A dermoscopic photograph of a skin lesion.
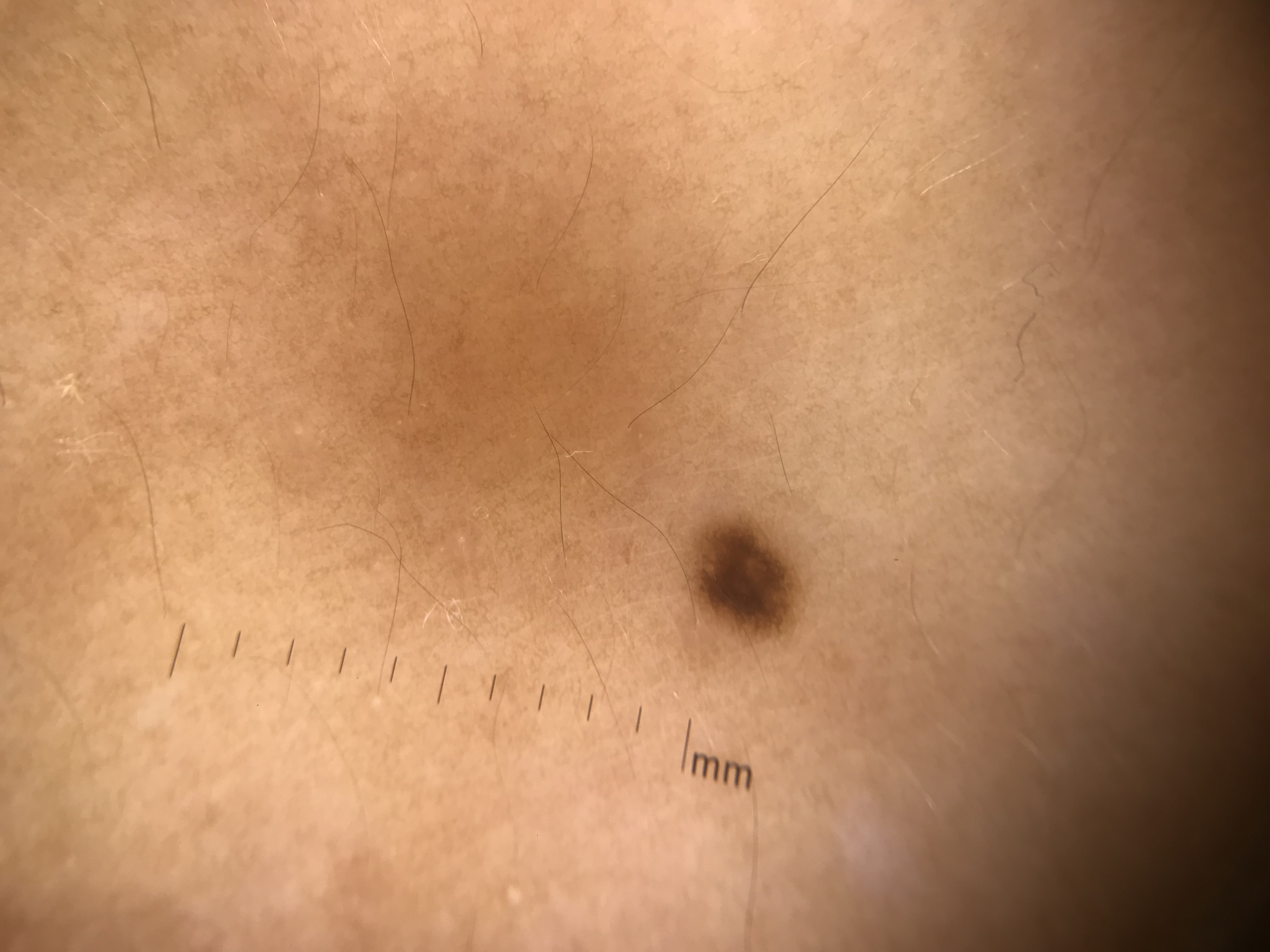diagnosis = junctional nevus (expert consensus)